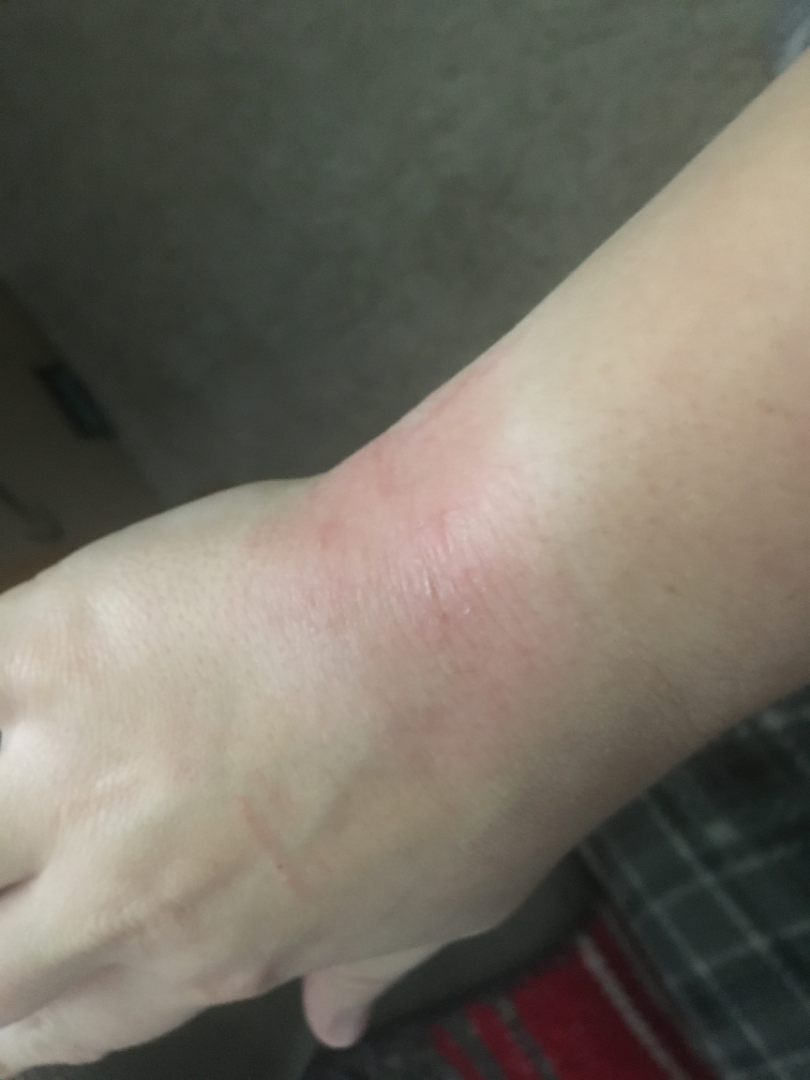shot_type: at an angle
patient: female, age 18–29
skin_tone:
  fitzpatrick: I
differential:
  leading:
    - Eczema
  considered:
    - Irritant Contact Dermatitis